The patient is a female in their 40s. A dermoscopy image of a single skin lesion:
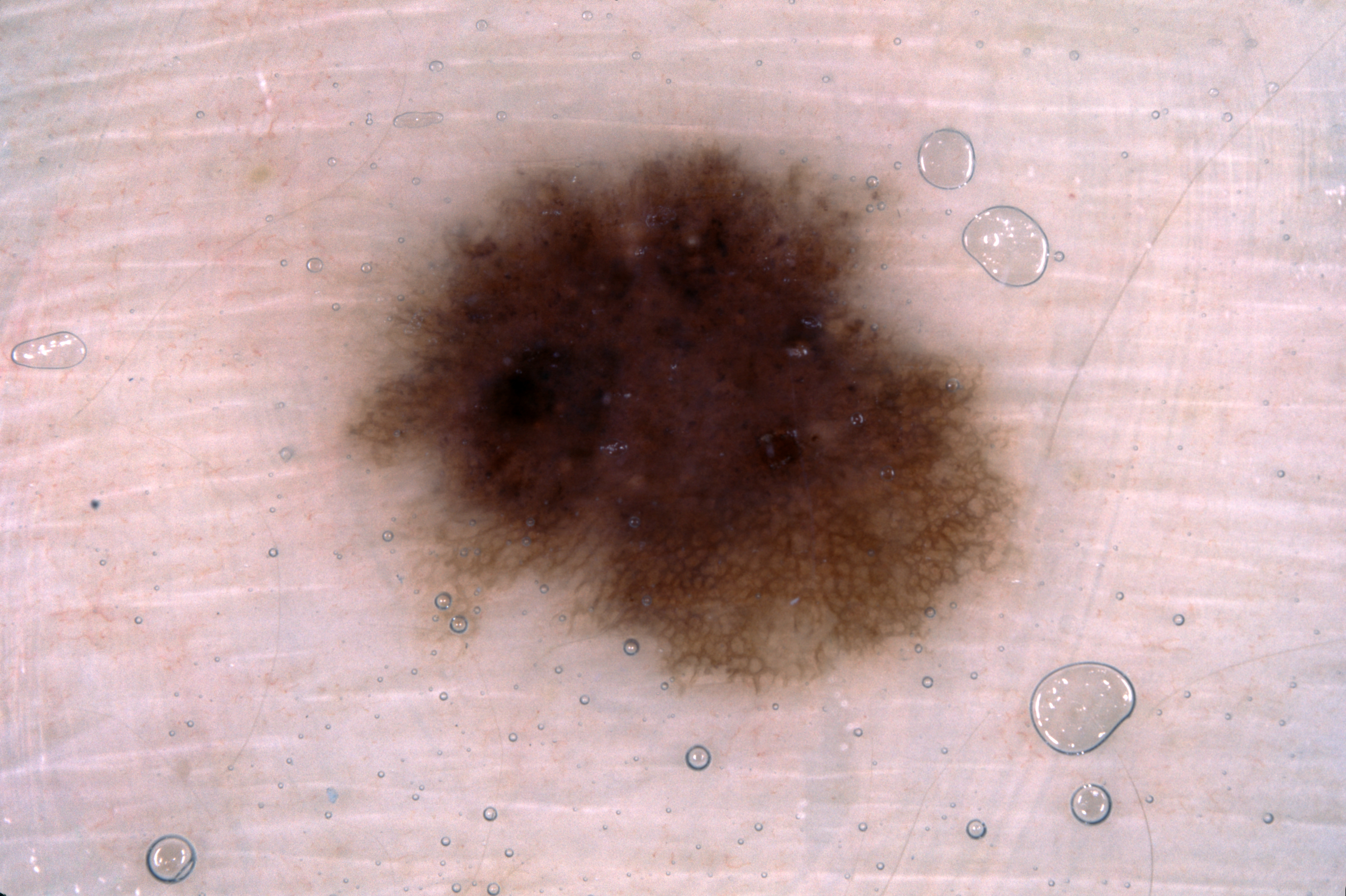Findings:
Dermoscopic review identifies pigment network. The lesion occupies the region 347/140/1020/693. The lesion occupies roughly 22% of the field.
Impression:
The clinical diagnosis was a melanocytic nevus, a benign lesion.